Dermoscopy of a skin lesion: 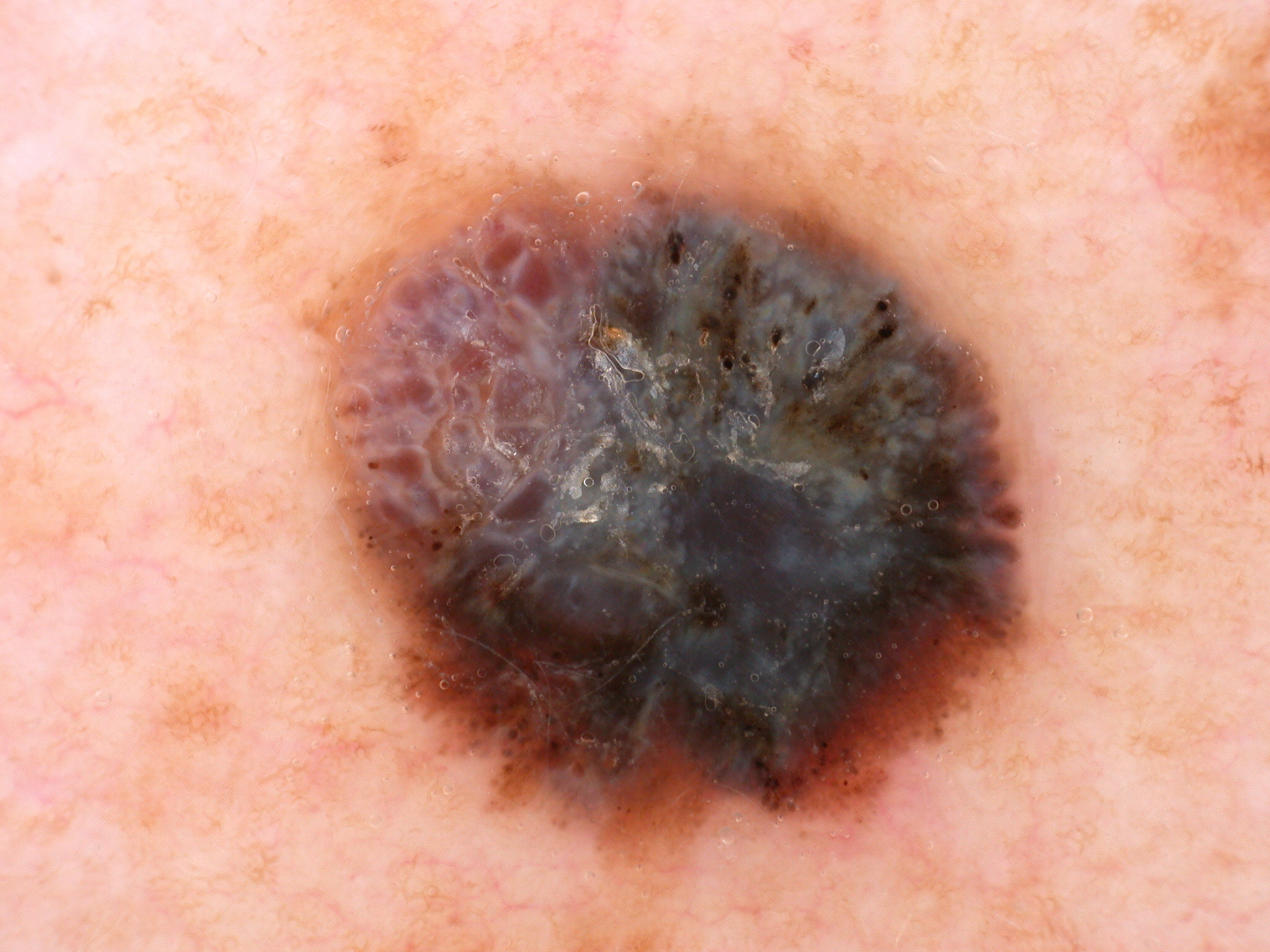Findings: Dermoscopic assessment notes globules, pigment network, and streaks, with no milia-like cysts or negative network. The lesion spans x1=292, y1=141, x2=1058, y2=861. Conclusion: Histopathologically confirmed as a melanoma.